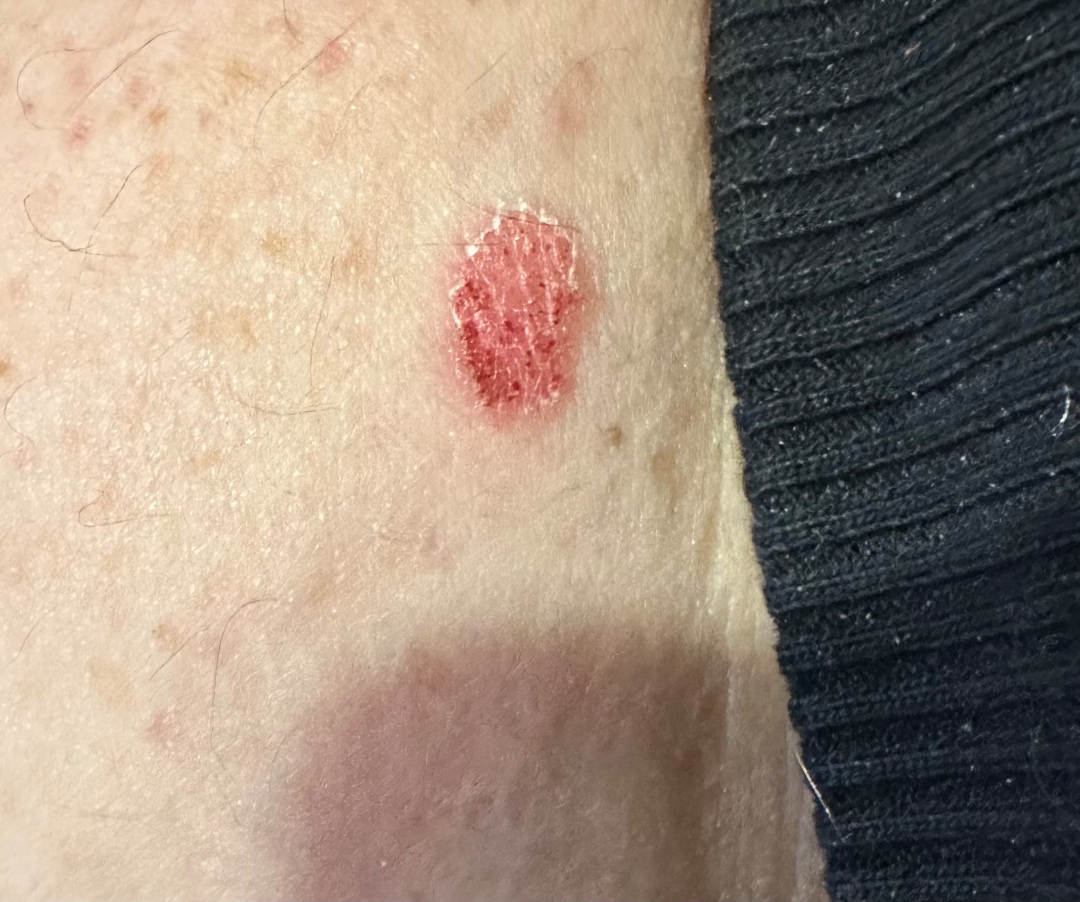Assessment: The reviewing dermatologist's impression was: Eczema (primary); Basal Cell Carcinoma (possible).